The leg is involved · female contributor, age 40–49 · this is a close-up image.
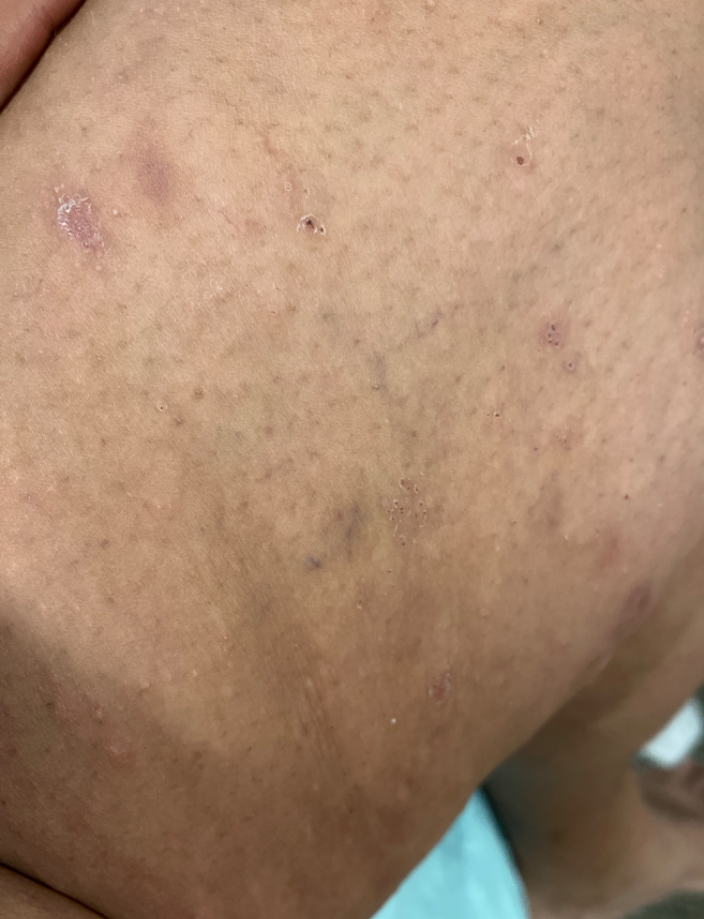Impression:
On independent review by the dermatologists, Eczema (favored); Pityriasis rosea (less likely); Allergic Contact Dermatitis (less likely); Lichen Simplex Chronicus (less likely); Folliculitis (less likely).